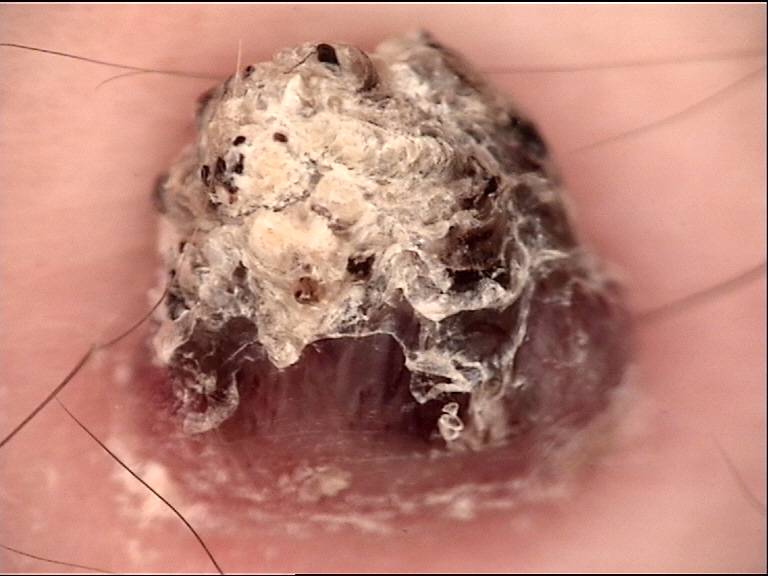<case>
  <image>dermoscopy</image>
  <lesion_type>
    <main_class>keratinocytic</main_class>
  </lesion_type>
  <diagnosis>
    <name>cutaneous horn</name>
    <code>ch</code>
    <malignancy>malignant</malignancy>
    <super_class>non-melanocytic</super_class>
    <confirmation>histopathology</confirmation>
  </diagnosis>
</case>